The lesion involves the top or side of the foot and leg · the photo was captured at a distance · the subject is a female aged 40–49: 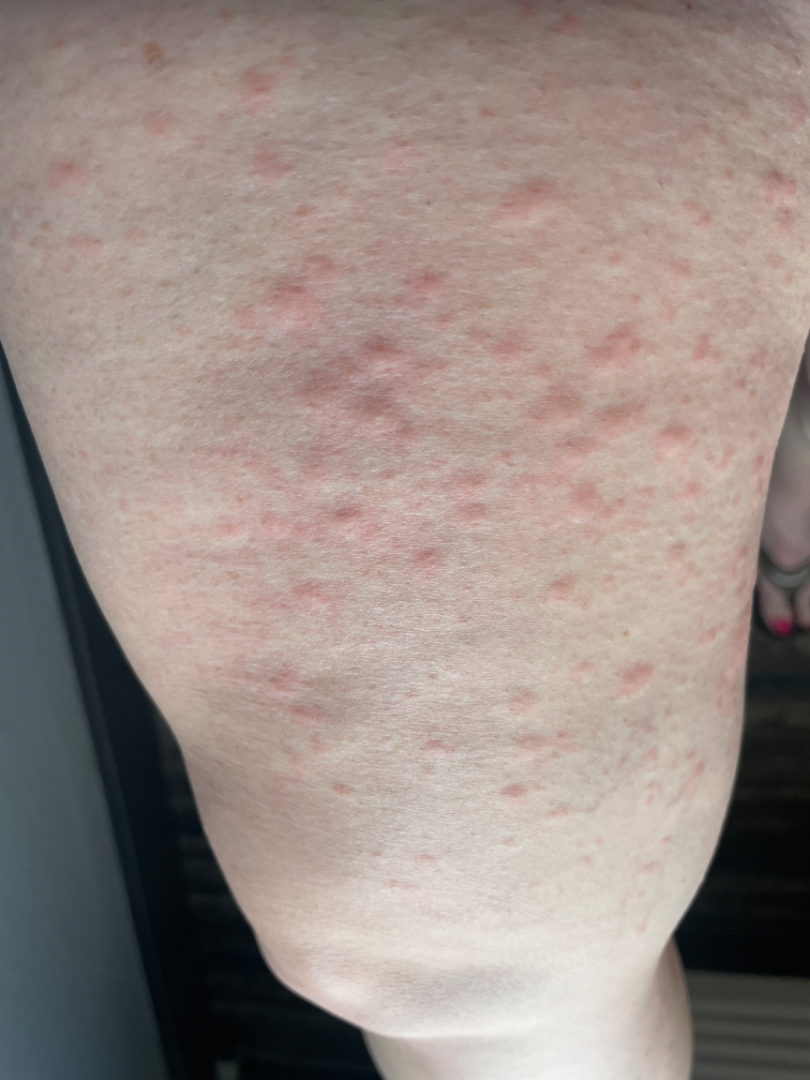| field | value |
|---|---|
| diagnostic considerations | Urticaria (favored); Eczema (remote); Allergic Contact Dermatitis (remote); Viral Exanthem (remote); Hypersensitivity (remote) |